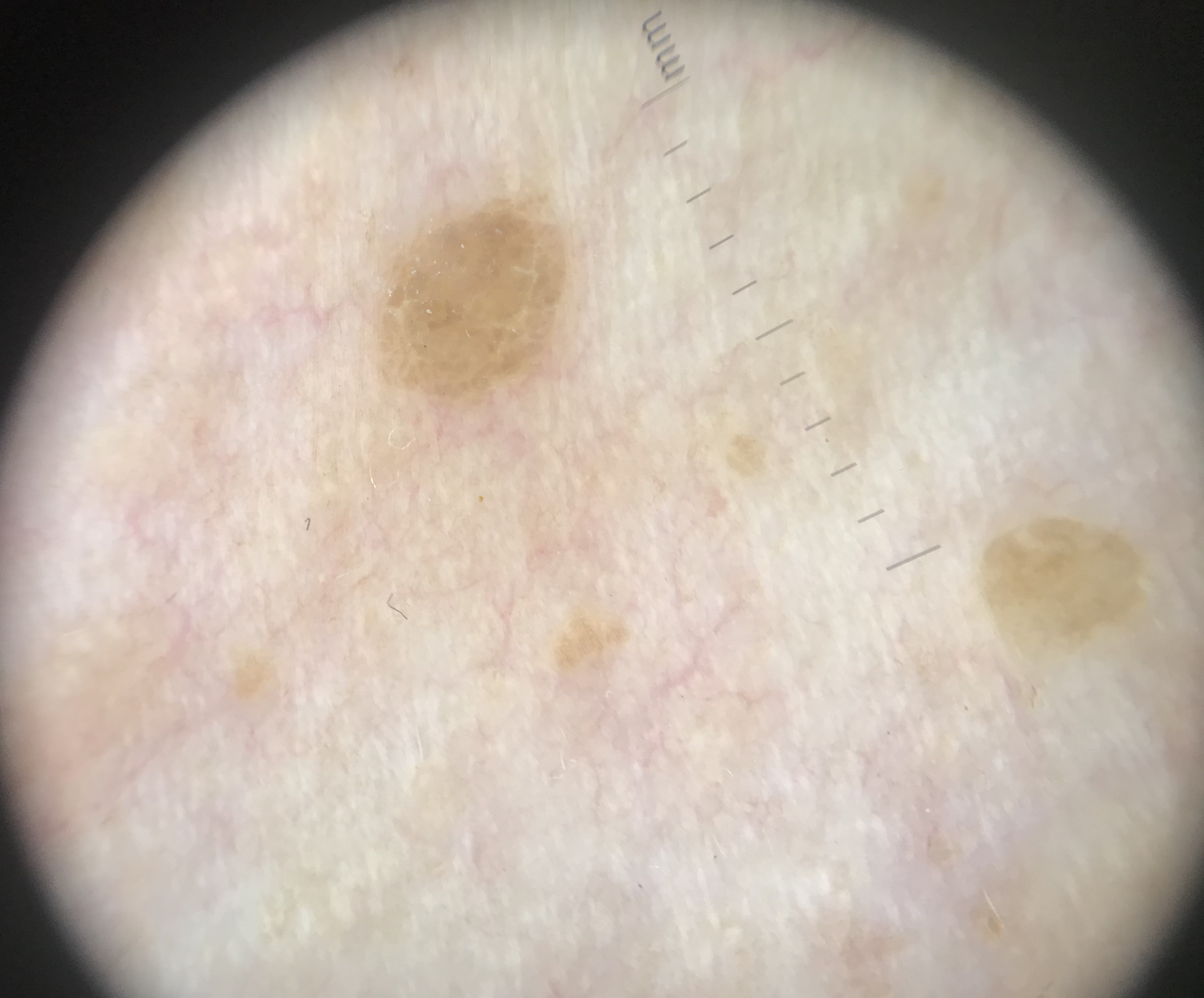{"diagnosis": {"name": "seborrheic keratosis", "code": "sk", "malignancy": "benign", "super_class": "non-melanocytic", "confirmation": "expert consensus"}}